This is a close-up image, the affected area is the arm and front of the torso: 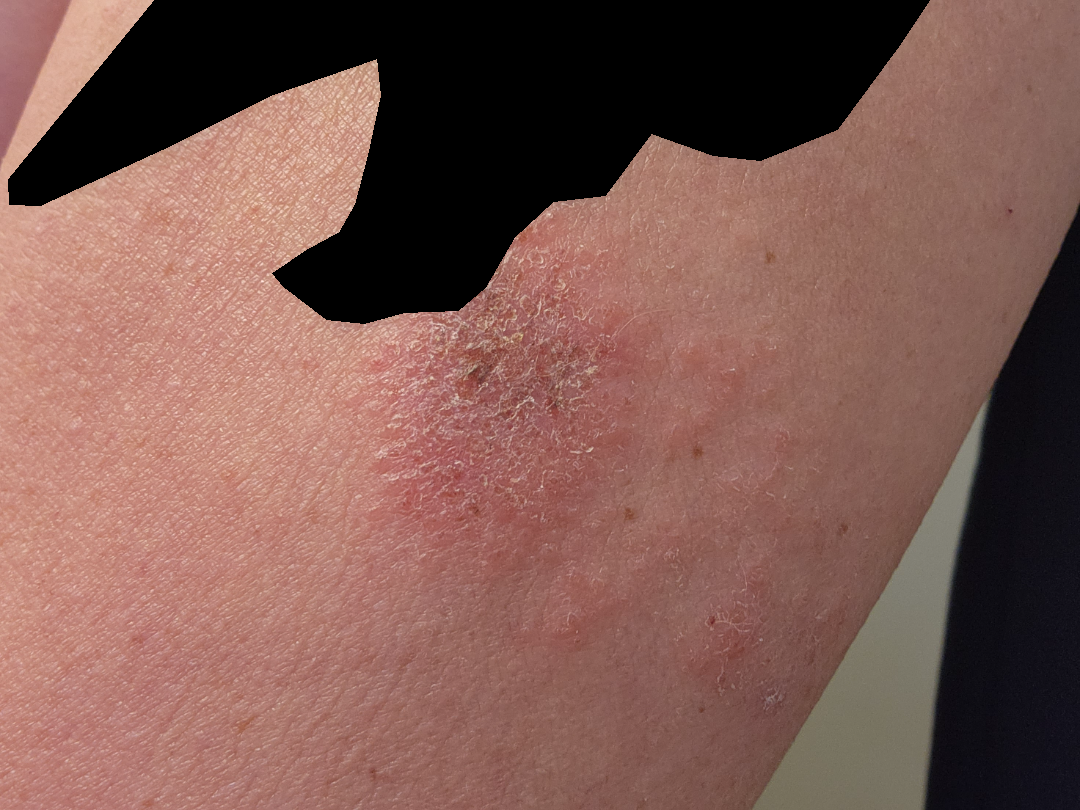<case>
  <patient_category>a rash</patient_category>
  <duration>one to three months</duration>
  <systemic_symptoms>none reported</systemic_symptoms>
  <symptoms>itching, burning, enlargement, bothersome appearance</symptoms>
  <texture>rough or flaky, raised or bumpy</texture>
  <differential>
    <leading>Eczema</leading>
  </differential>
</case>